The patient is a female aged 60–69. The photo was captured at a distance. Located on the head or neck, front of the torso, arm and palm: 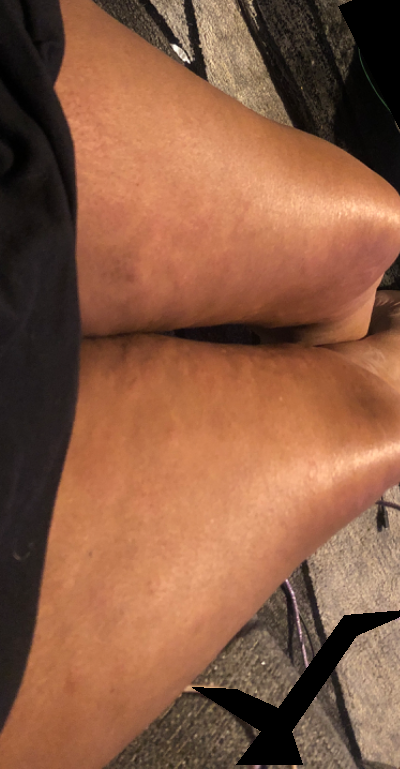The patient indicates the condition has been present for three to twelve months. The lesion is associated with itching. Texture is reported as raised or bumpy. Skin tone: Fitzpatrick phototype IV; lay reviewers estimated Monk Skin Tone 4 or 7. The patient reported no systemic symptoms. The patient described the issue as a rash. On dermatologist assessment of the image, Urticaria and Leukocytoclastic Vasculitis were considered with similar weight.